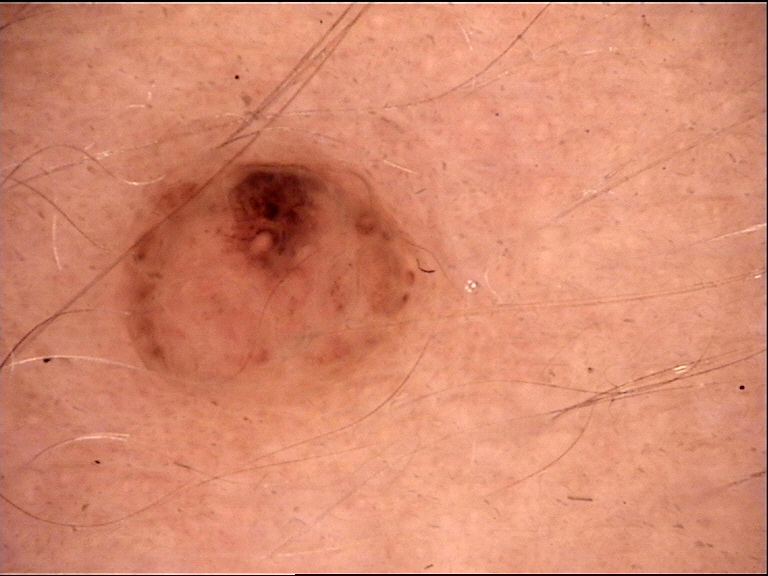A dermatoscopic image of a skin lesion. The architecture is that of a banal lesion. The diagnostic label was a dermal nevus.